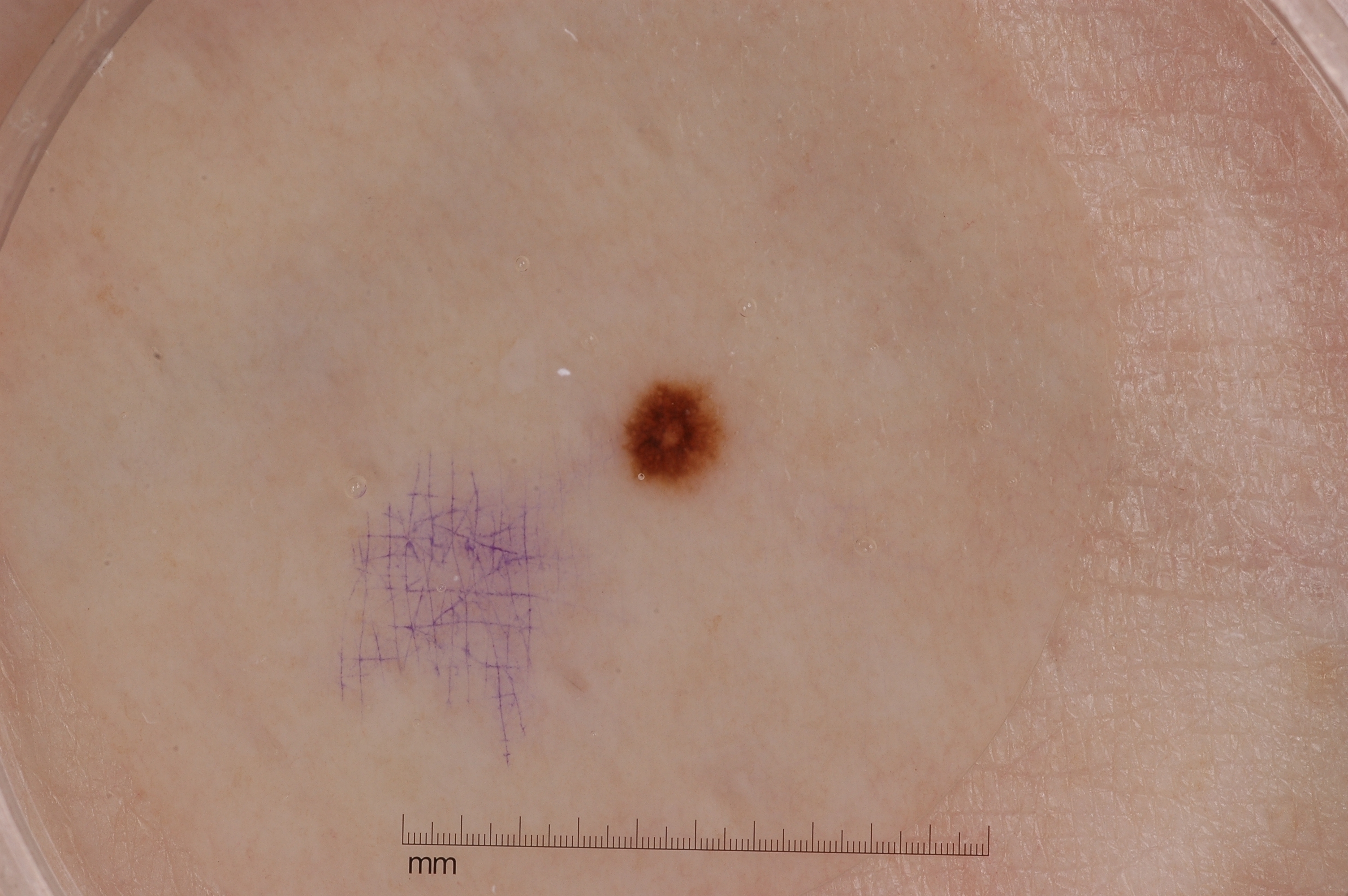{"image": {"modality": "dermoscopy"}, "patient": {"sex": "female", "age_approx": 50}, "lesion_extent": {"approx_field_fraction_pct": 1}, "dermoscopic_features": {"present": ["pigment network"], "absent": ["streaks", "negative network", "milia-like cysts"]}, "lesion_location": {"bbox_xyxy": [611, 371, 737, 497]}, "diagnosis": {"name": "melanocytic nevus", "malignancy": "benign", "lineage": "melanocytic", "provenance": "clinical"}}